This is a close-up image; self-categorized by the patient as a rash; texture is reported as raised or bumpy; the patient indicates associated fatigue and shortness of breath; the lesion is associated with itching, bothersome appearance and pain; the lesion involves the head or neck.
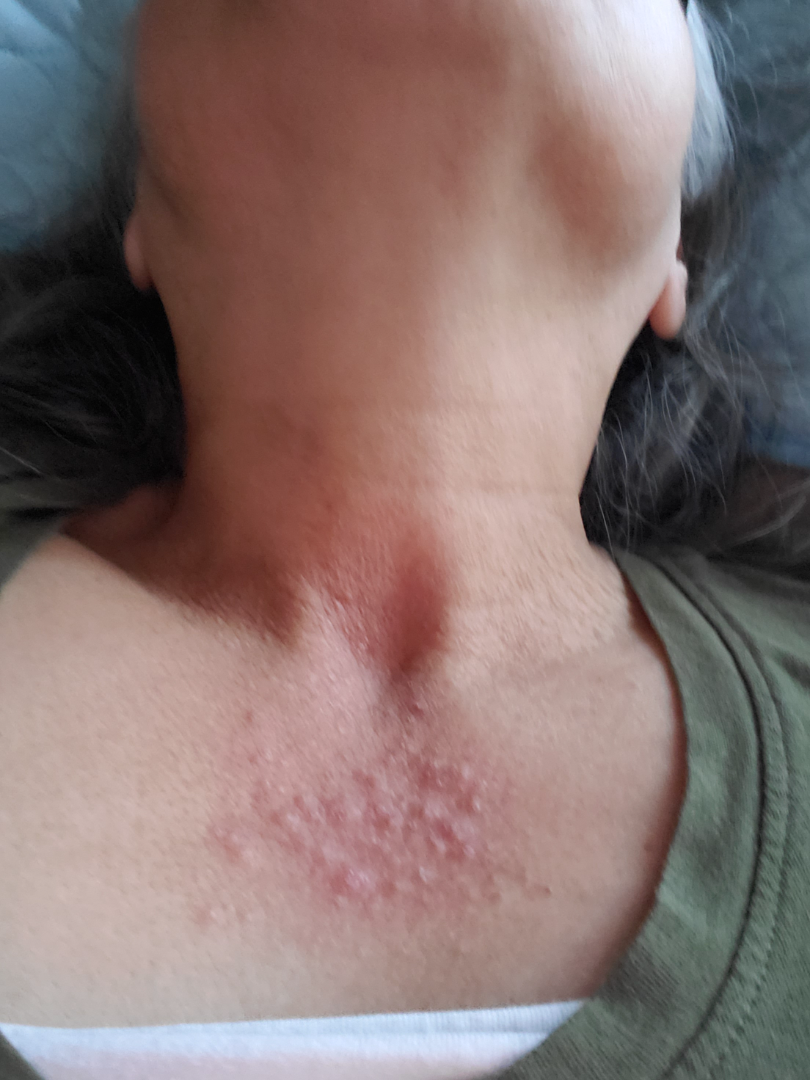Assessment:
On photographic review by a dermatologist, Cutaneous lupus (weight 0.55); Lichenified eczematous dermatitis (weight 0.27); Dermatomyositis (weight 0.18).